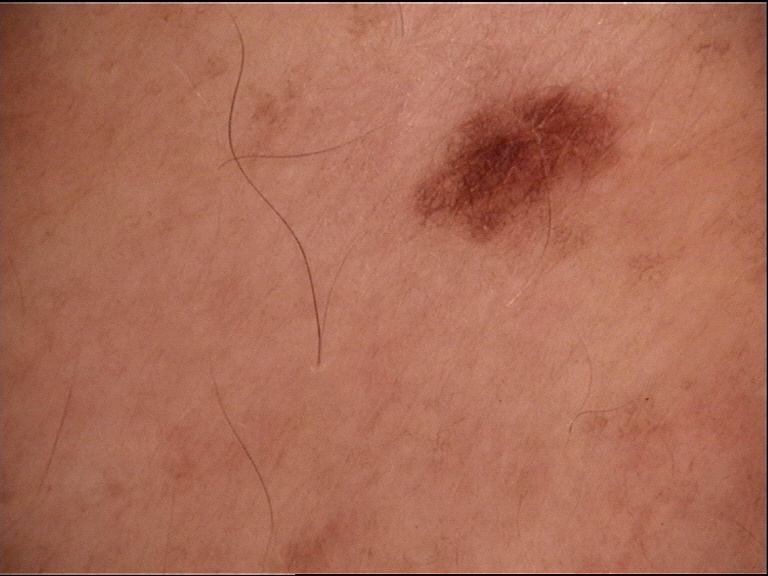A dermoscopic close-up of a skin lesion. The diagnosis was a dysplastic junctional nevus.